A dermoscopy image of a single skin lesion: 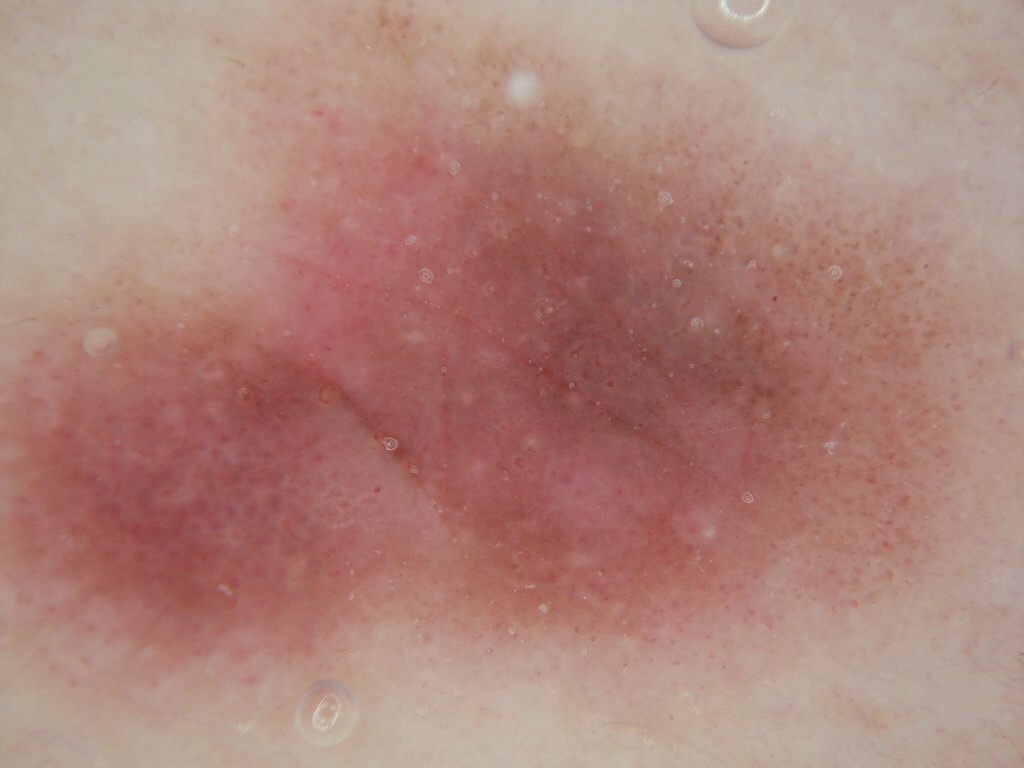The lesion extends across the full dermoscopic field. Consistent with a benign skin lesion.